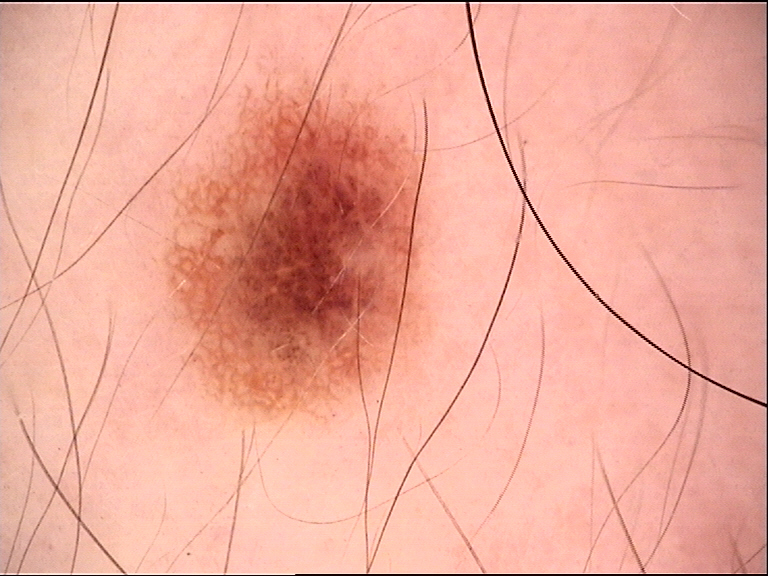modality = dermatoscopy, diagnostic label = dysplastic junctional nevus (expert consensus).